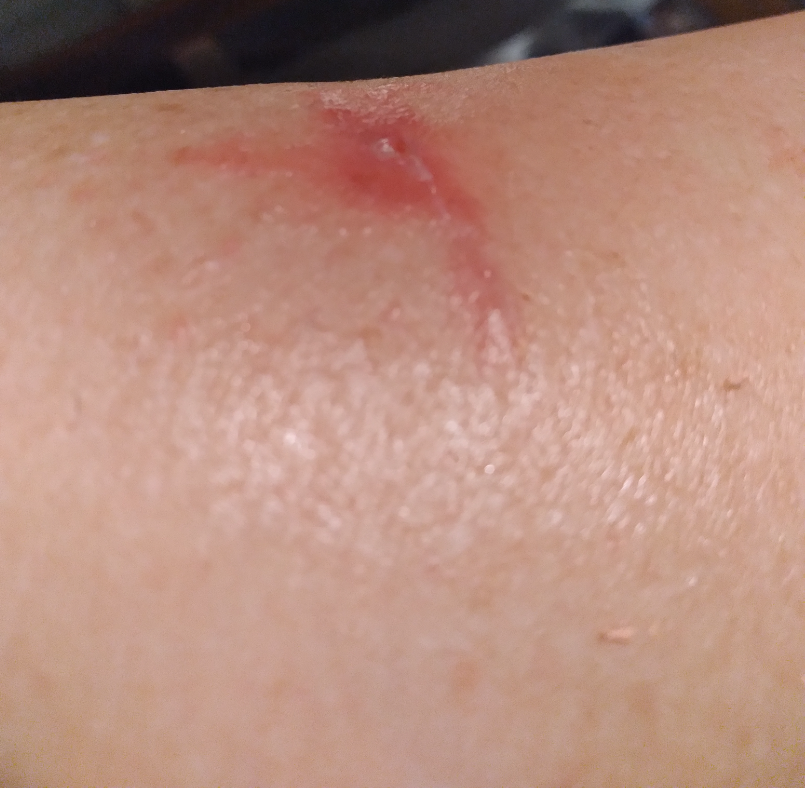Findings:
• assessment · not assessable
• patient · female, age 40–49
• framing · at an angle
• anatomic site · leg